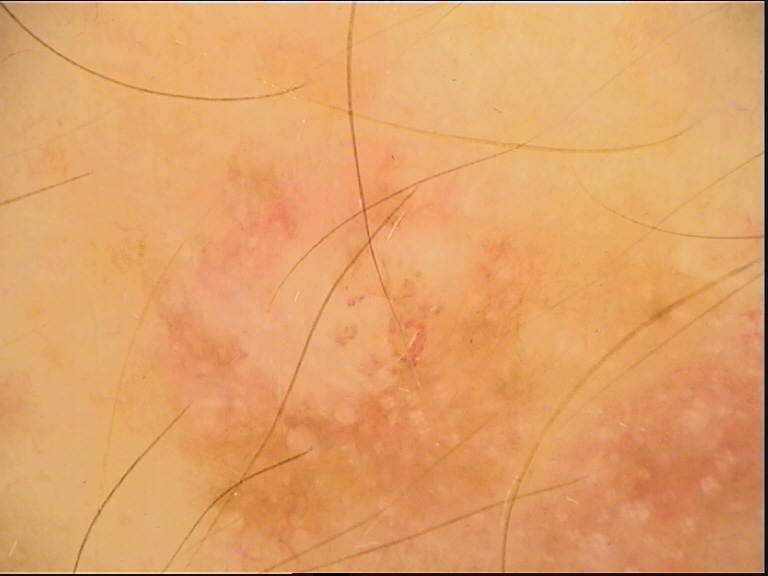<case>
<diagnosis>
<name>actinic keratosis</name>
<code>ak</code>
<malignancy>indeterminate</malignancy>
<super_class>non-melanocytic</super_class>
<confirmation>expert consensus</confirmation>
</diagnosis>
</case>